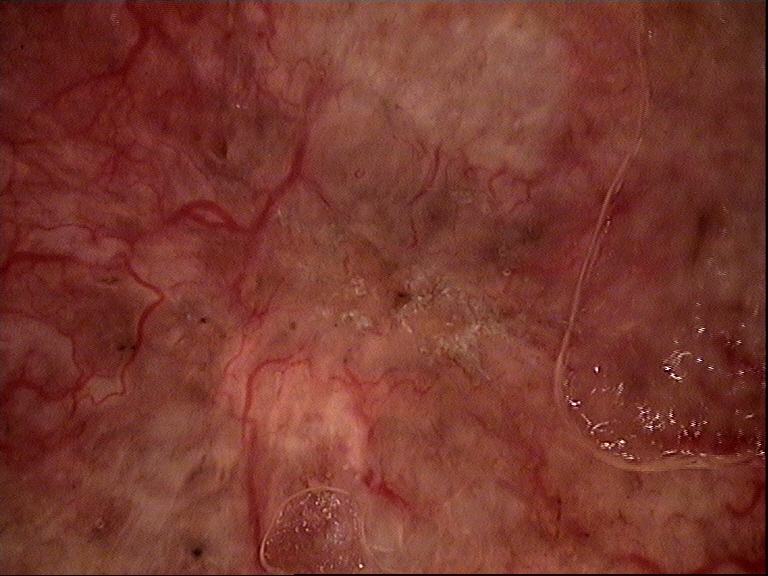modality — dermoscopy; label — basal cell carcinoma (biopsy-proven).